A dermoscopic photograph of a skin lesion.
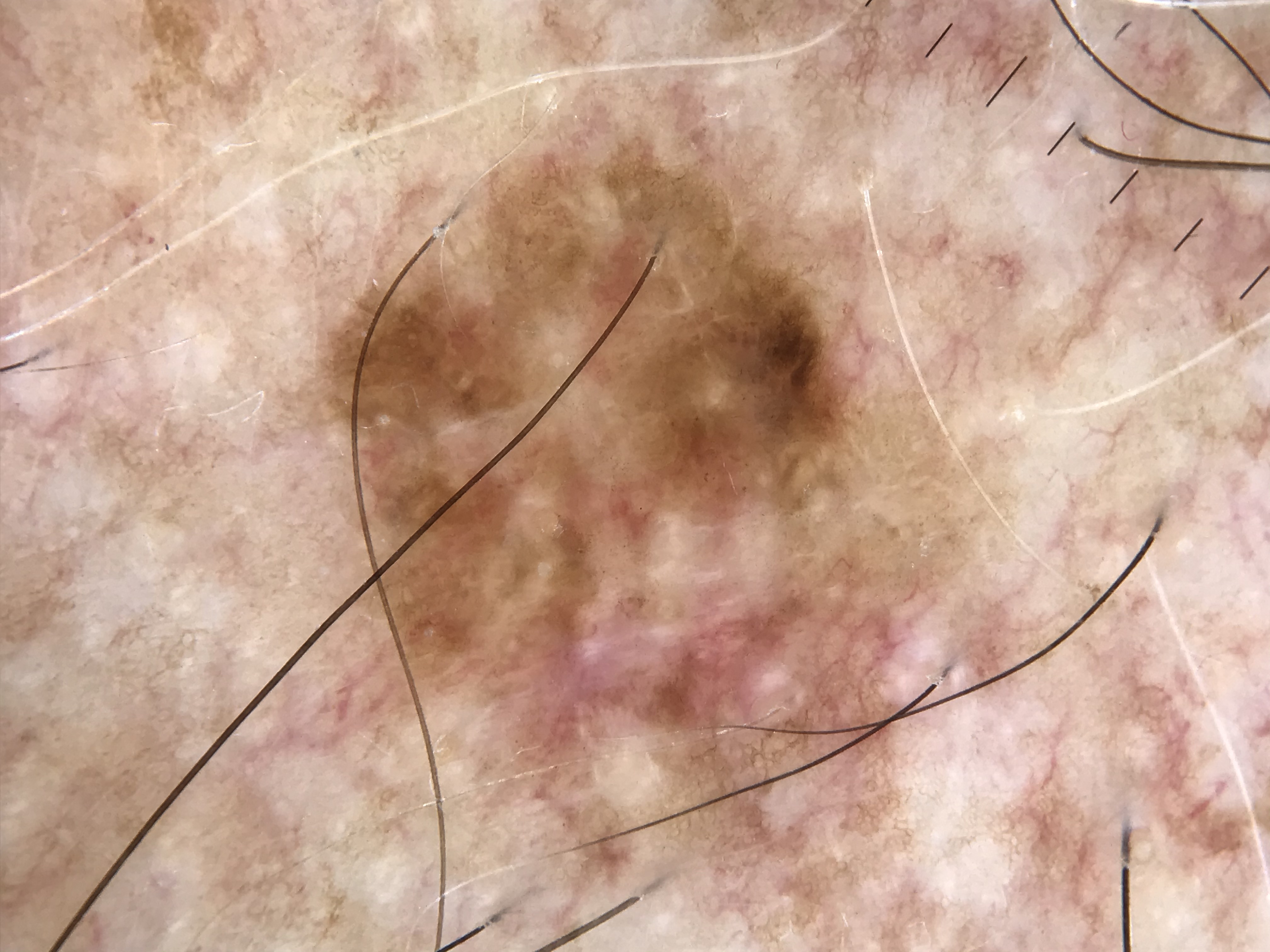Histopathology confirmed a malignant lesion — a melanoma.